A dermoscopy image of a single skin lesion.
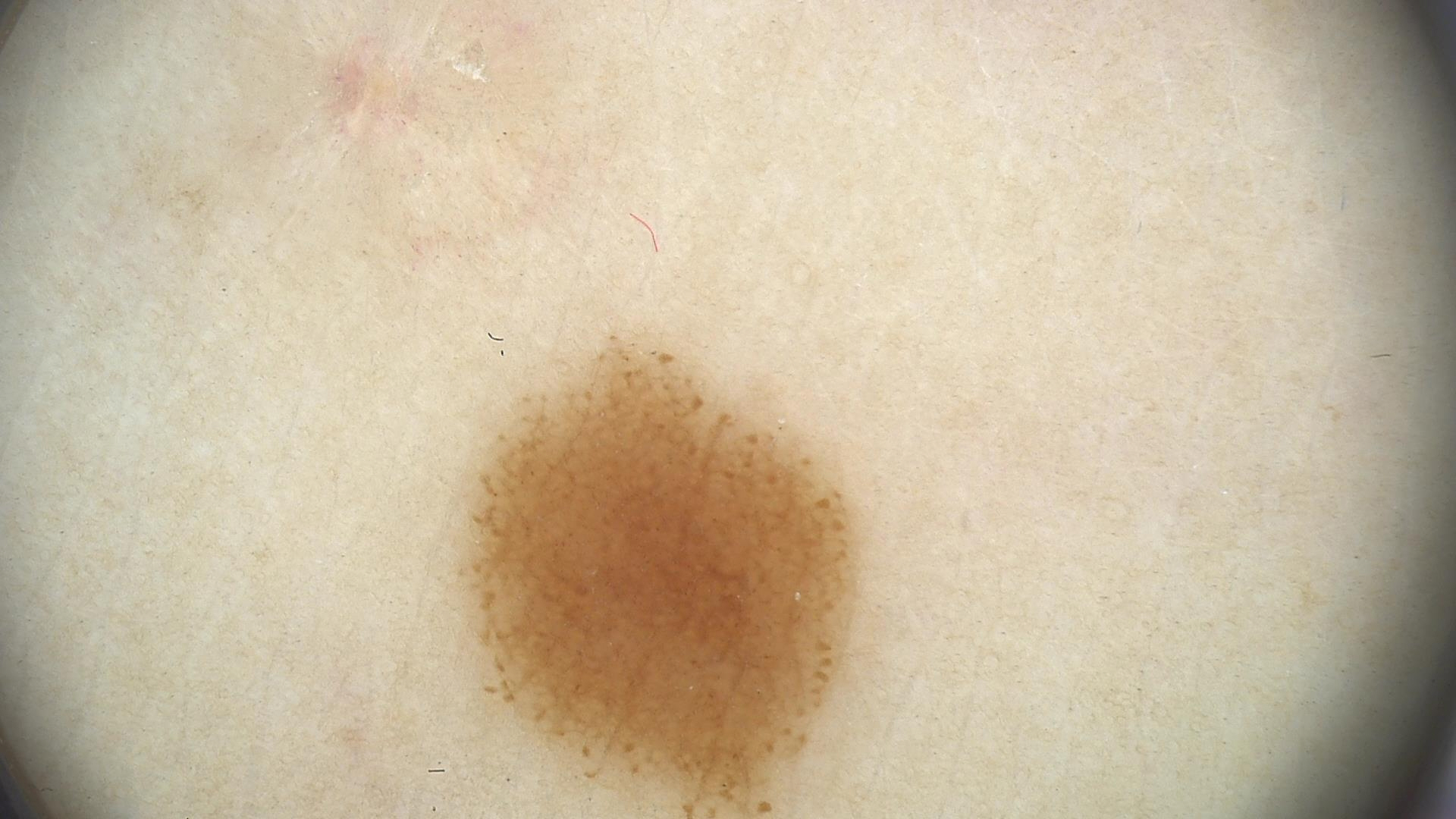<lesion>
<diagnosis>
<name>dysplastic junctional nevus</name>
<code>jd</code>
<malignancy>benign</malignancy>
<super_class>melanocytic</super_class>
<confirmation>expert consensus</confirmation>
</diagnosis>
</lesion>